This image was taken at an angle; the leg, head or neck and arm are involved: 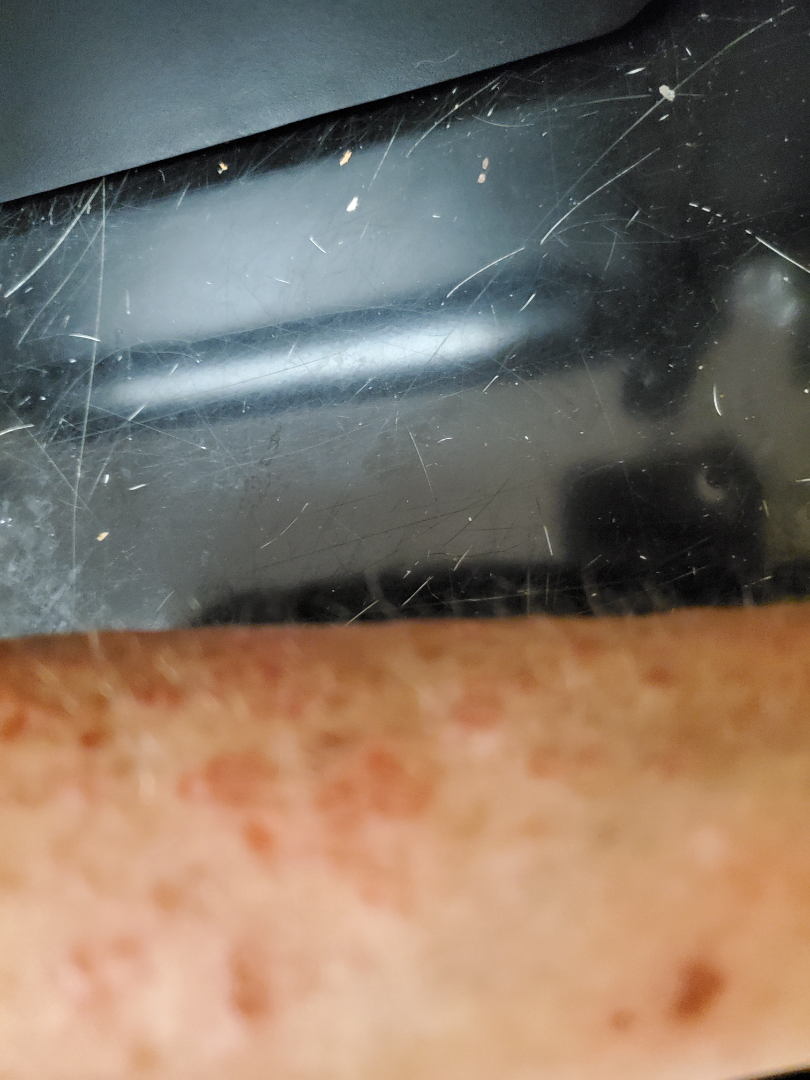<dermatology_case>
<assessment>could not be assessed</assessment>
<patient_category>a rash</patient_category>
<duration>less than one week</duration>
<systemic_symptoms>none reported</systemic_symptoms>
<texture>raised or bumpy</texture>
</dermatology_case>